A dermoscopy image of a single skin lesion.
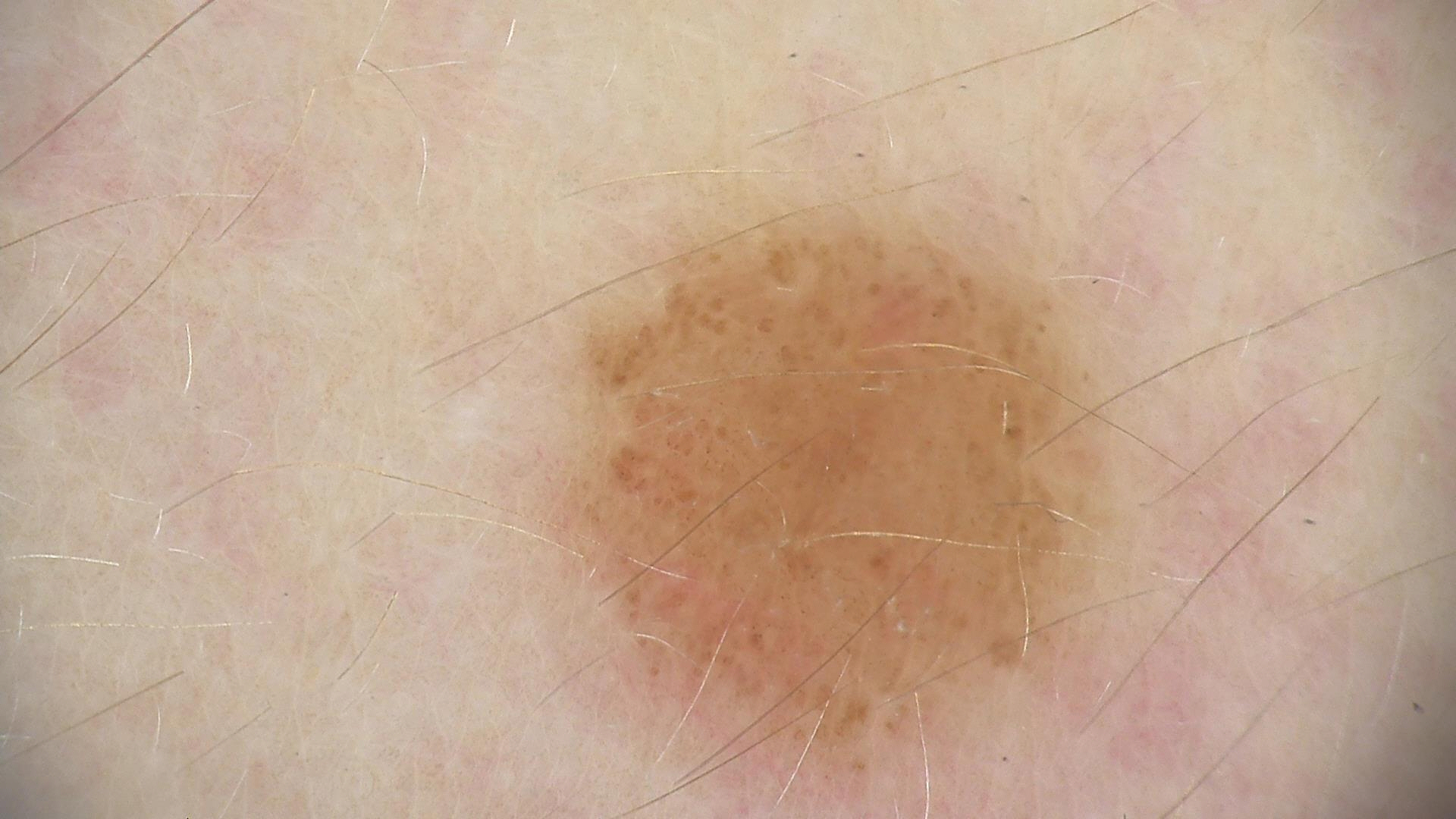Conclusion:
Consistent with a banal lesion — a compound nevus.